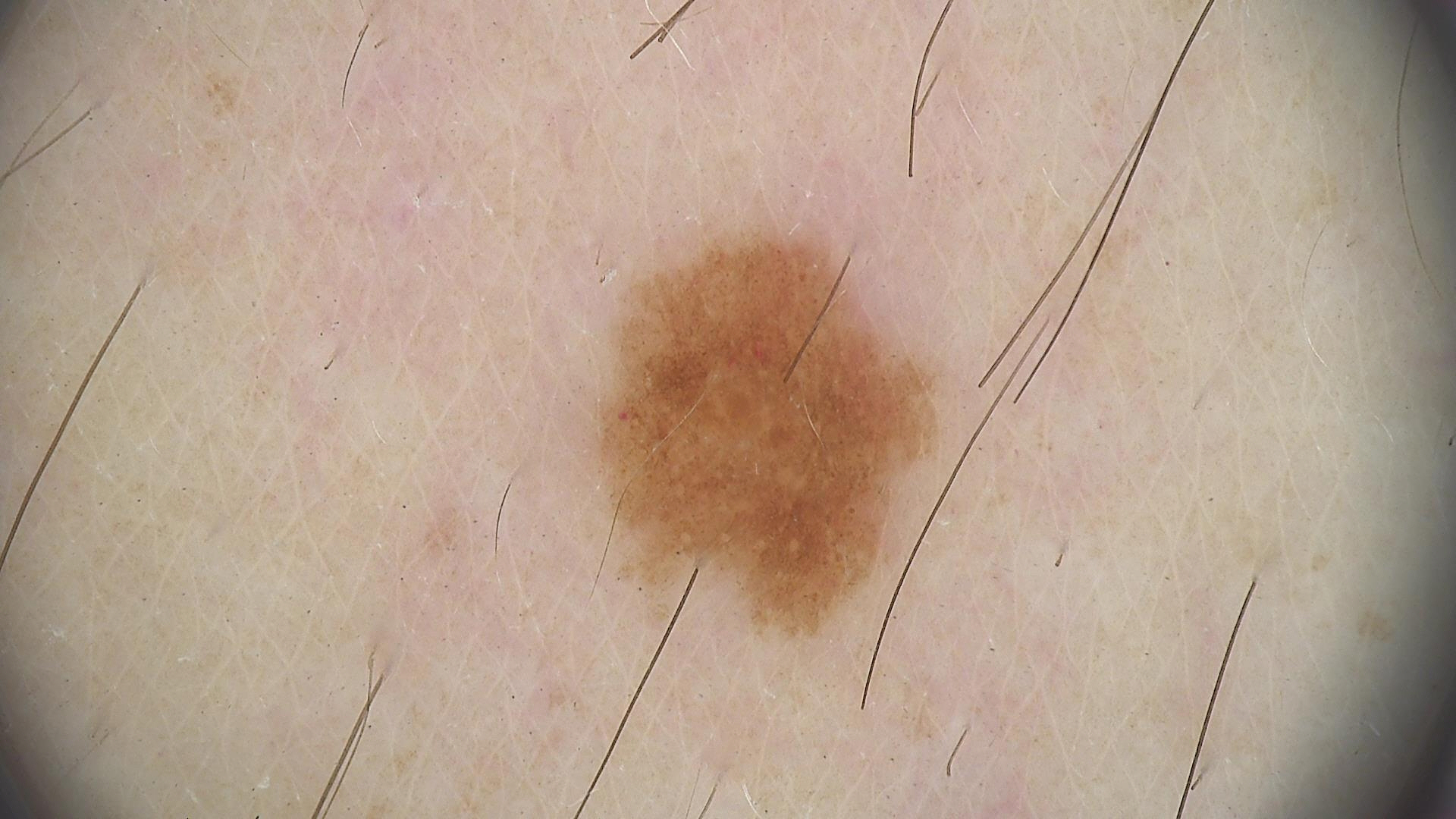Q: What is this lesion?
A: dysplastic junctional nevus (expert consensus)